A dermatoscopic image of a skin lesion:
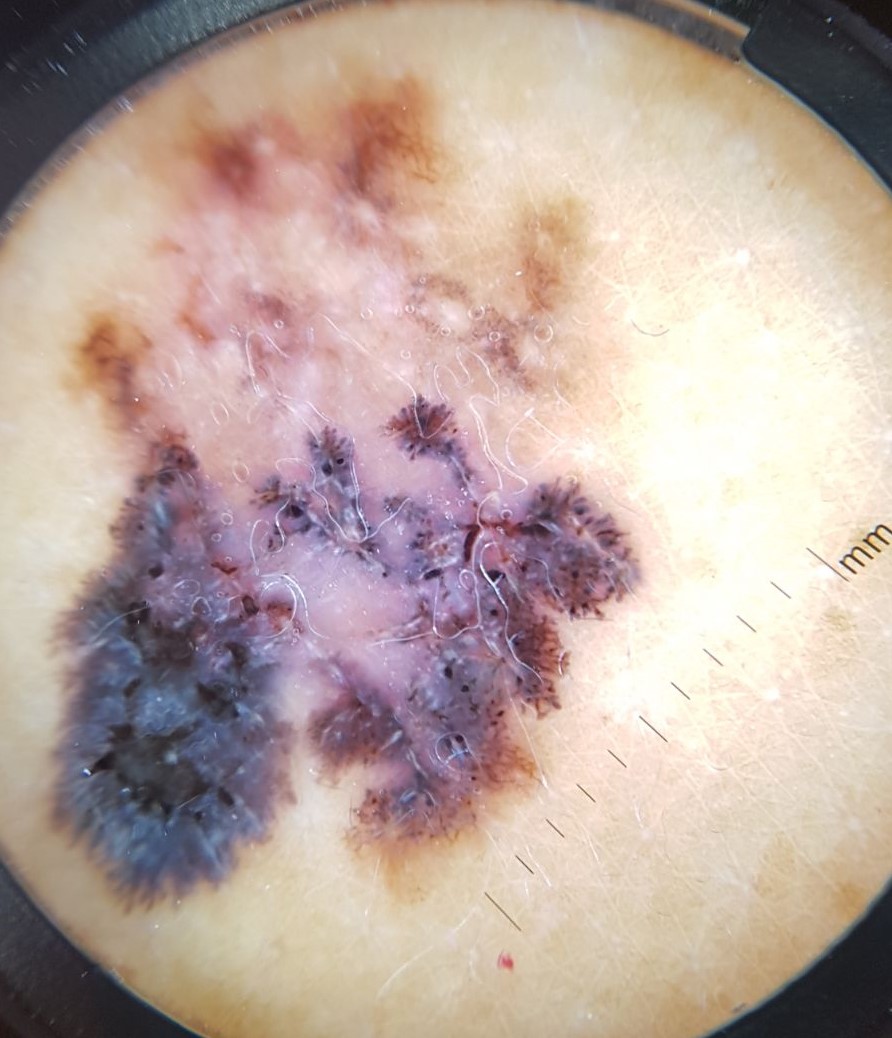| key | value |
|---|---|
| pathology | melanoma (biopsy-proven) |